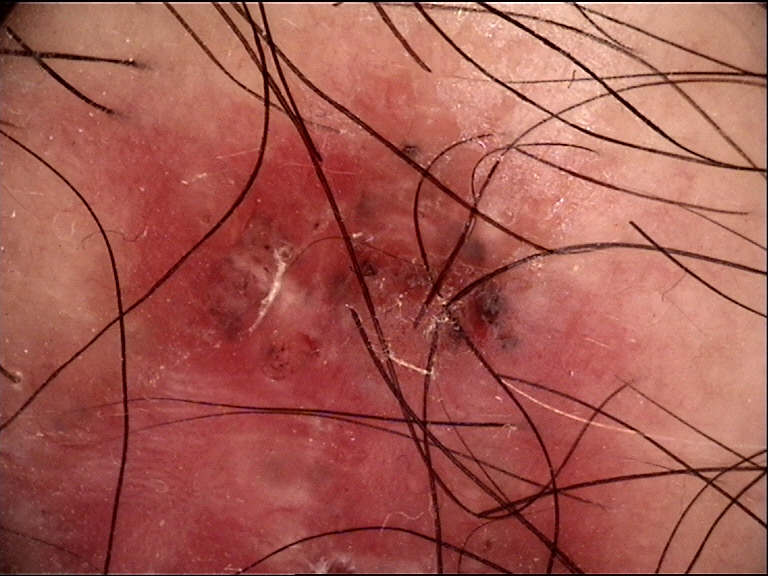A dermoscopic photograph of a skin lesion. The architecture is that of a keratinocytic lesion. Biopsy-confirmed as a basal cell carcinoma.